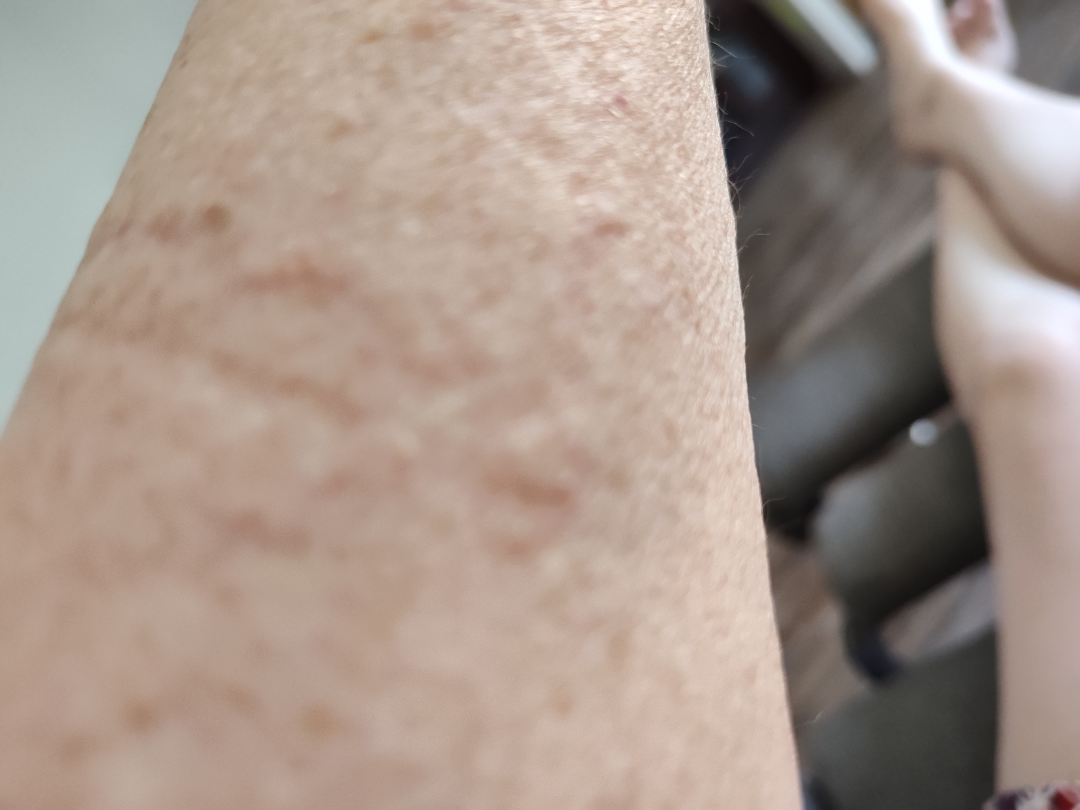Clinical context:
The lesion is described as raised or bumpy. The patient is 60–69, female. An image taken at an angle. The patient reports itching. The patient reports the condition has been present for about one day. The patient described the issue as a rash. Located on the arm.
Assessment:
On remote dermatologist review: Eczema (primary); Irritant Contact Dermatitis (possible); Pigmented purpuric eruption (remote); Allergic Contact Dermatitis (remote).